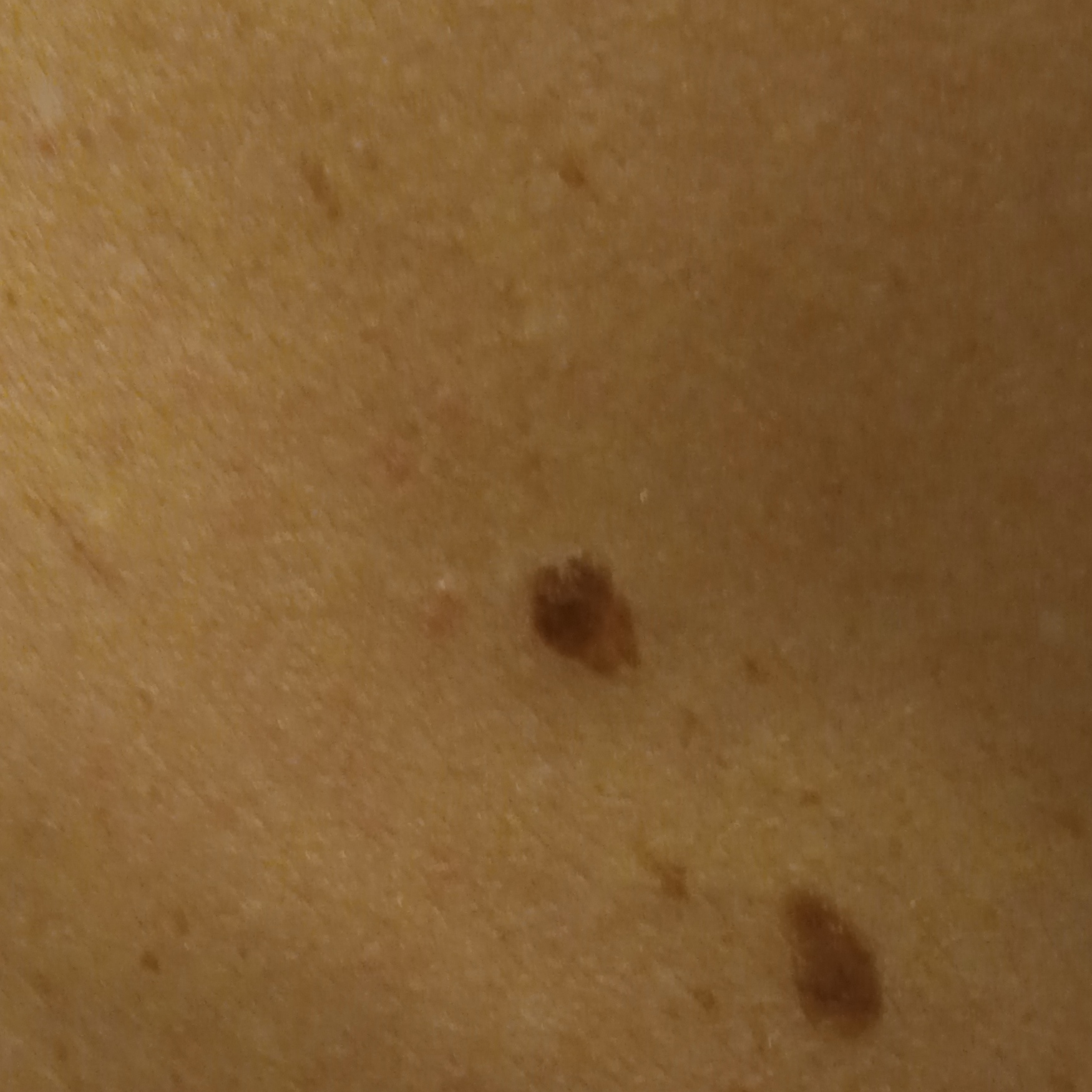sun reaction = skin tans without first burning | subject = male, 72 years of age | referral context = research study (no referral diagnosis) | image = clinical photo | body site = the back | size = 9.6 mm | diagnostic label = seborrheic keratosis (dermatologist consensus).